A dermoscopic image of a skin lesion:
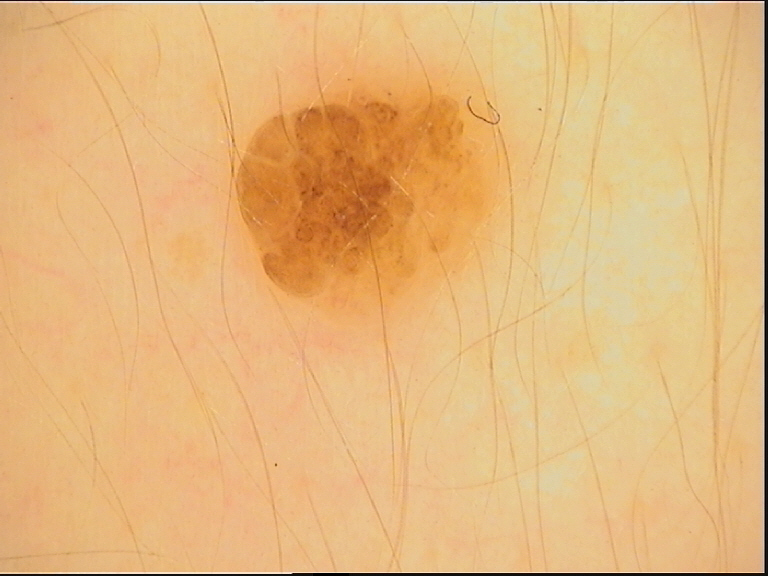The architecture is that of a banal lesion. Classified as a dermal nevus.